No associated systemic symptoms reported, the patient described the issue as a rash, the photograph was taken at a distance, located on the front of the torso, the patient is female.
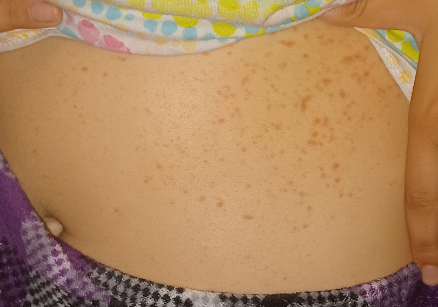Assessment: The reviewing dermatologists' impression was: Eczema and Grover's disease were each considered, in no particular order; less probable is Miliaria; lower on the differential is Folliculitis.